Dermoscopy of a skin lesion.
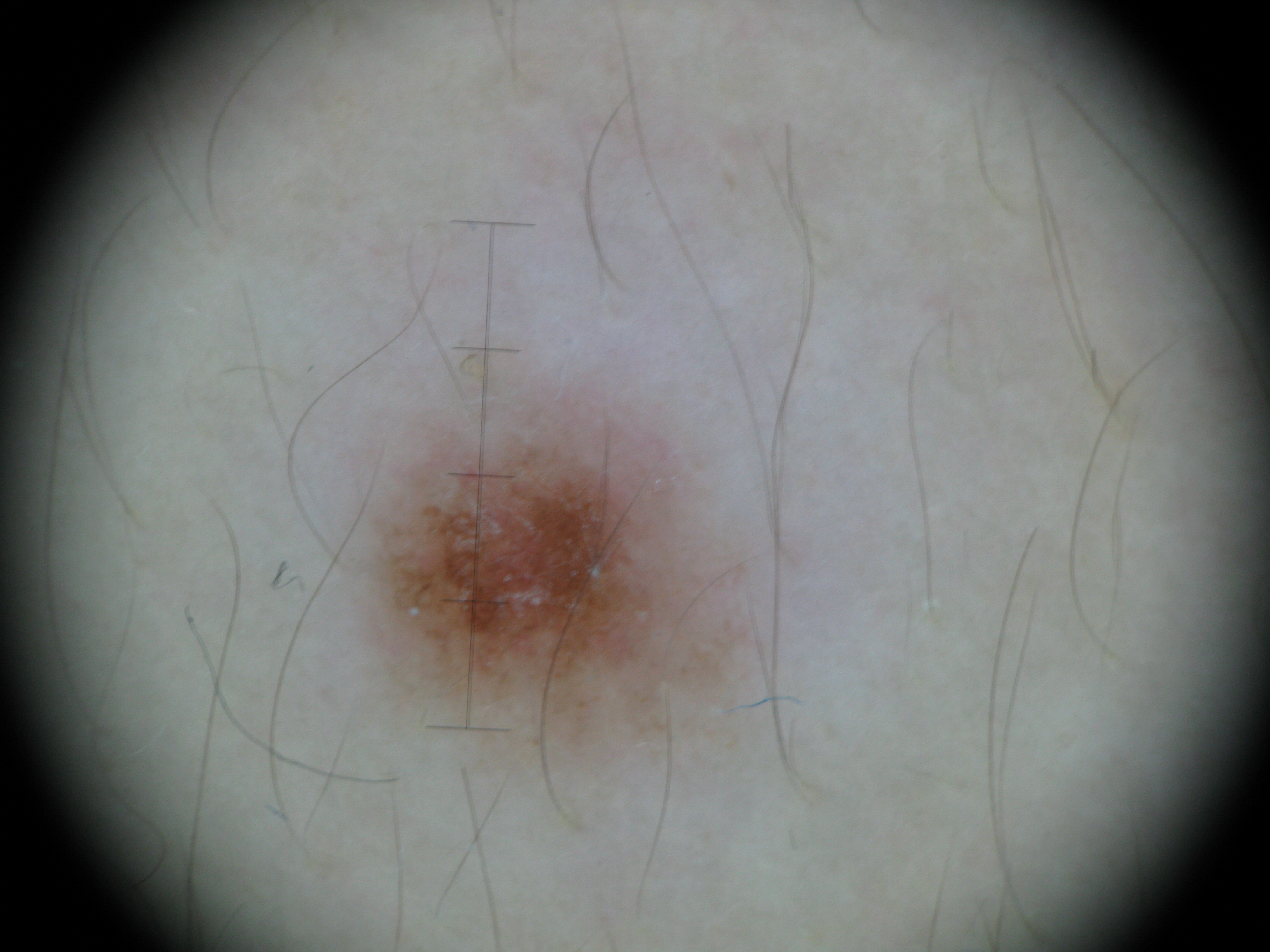Impression:
The diagnostic label was a benign lesion — a dysplastic junctional nevus.